Dermoscopy of a skin lesion; on a questionnaire the patient reported a personal history of skin cancer — 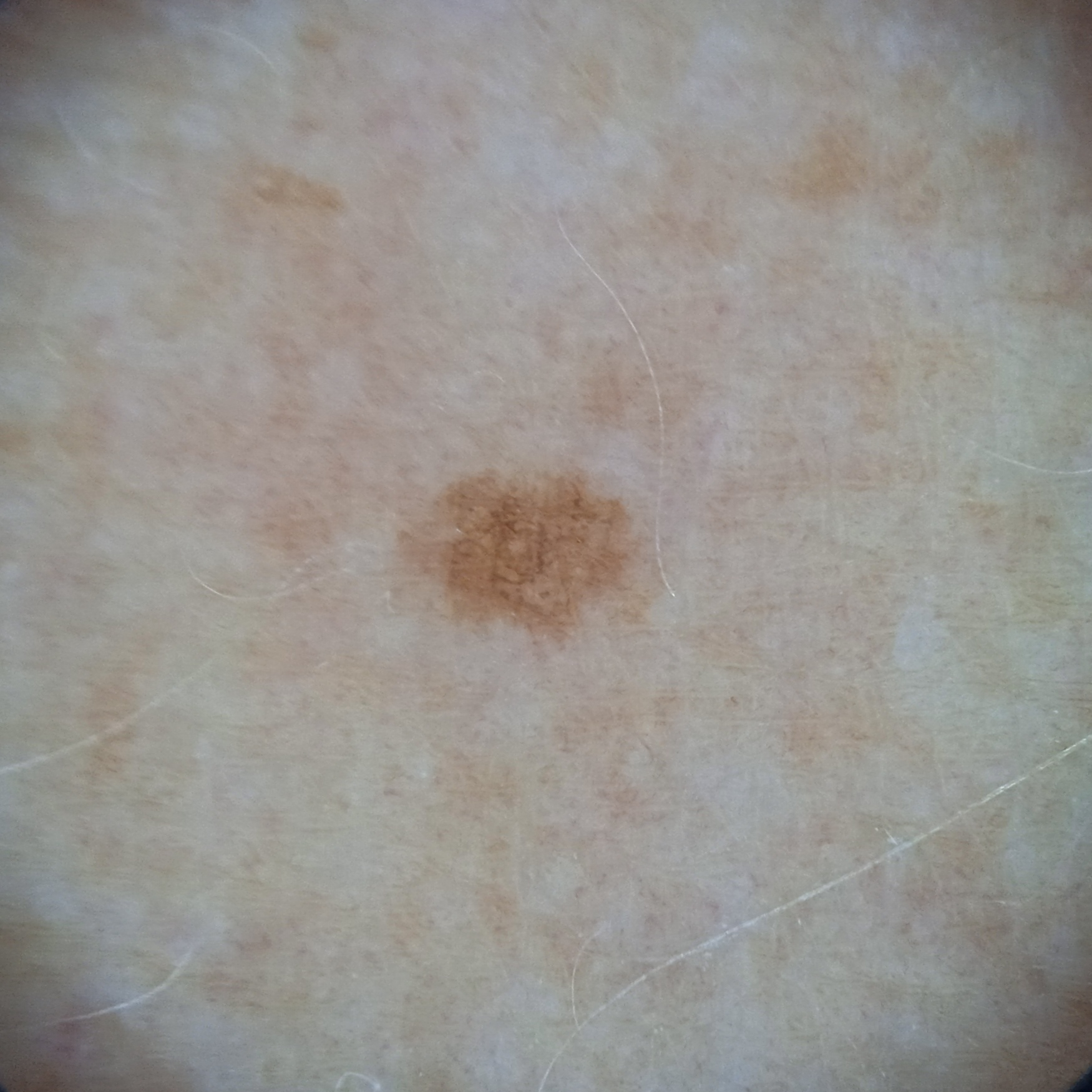* location — an arm
* diameter — 2.3 mm
* diagnosis — melanocytic nevus (dermatologist consensus)